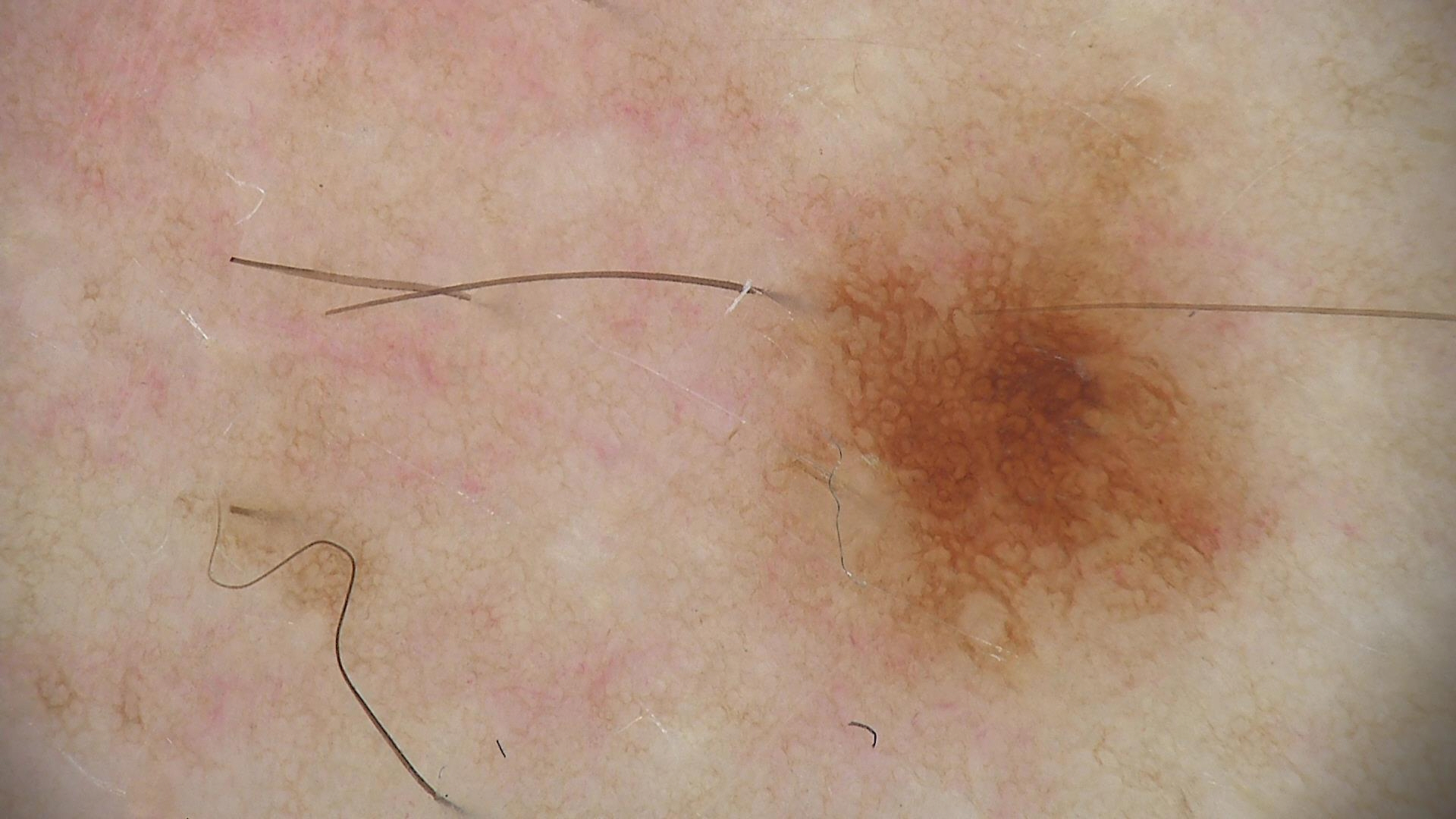image: dermoscopy | assessment: dysplastic junctional nevus (expert consensus).